Referred with a clinical suspicion of melanoma — 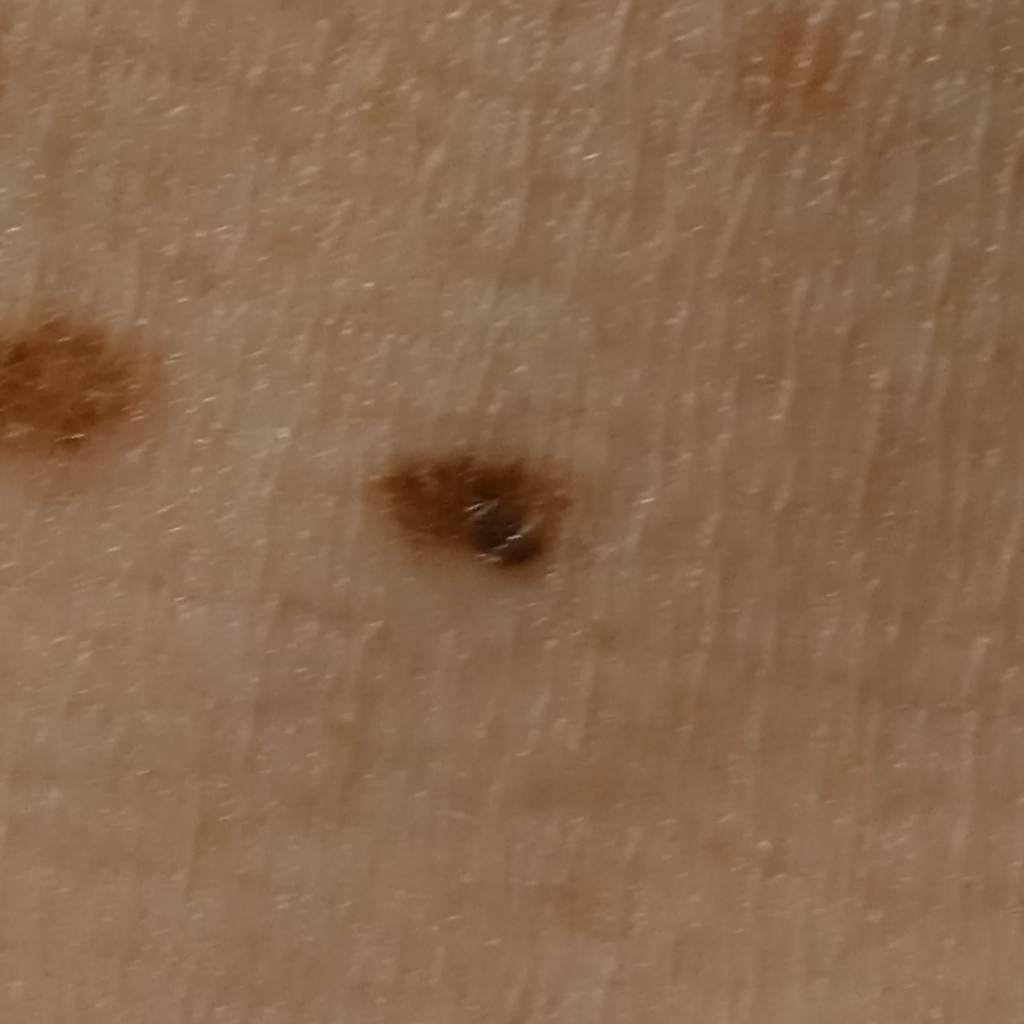<case>
  <lesion_size>
    <diameter_mm>5.2</diameter_mm>
  </lesion_size>
  <diagnosis>
    <name>melanocytic nevus</name>
    <malignancy>benign</malignancy>
    <procedure>excision</procedure>
  </diagnosis>
</case>